A male patient in their 70s. A clinical photo of a skin lesion taken with a smartphone — 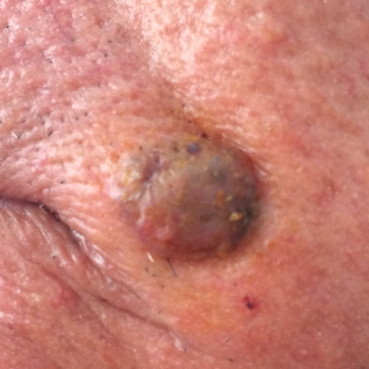anatomic site: the face | symptoms: bleeding, growth, itching, elevation | diagnosis: basal cell carcinoma (biopsy-proven).